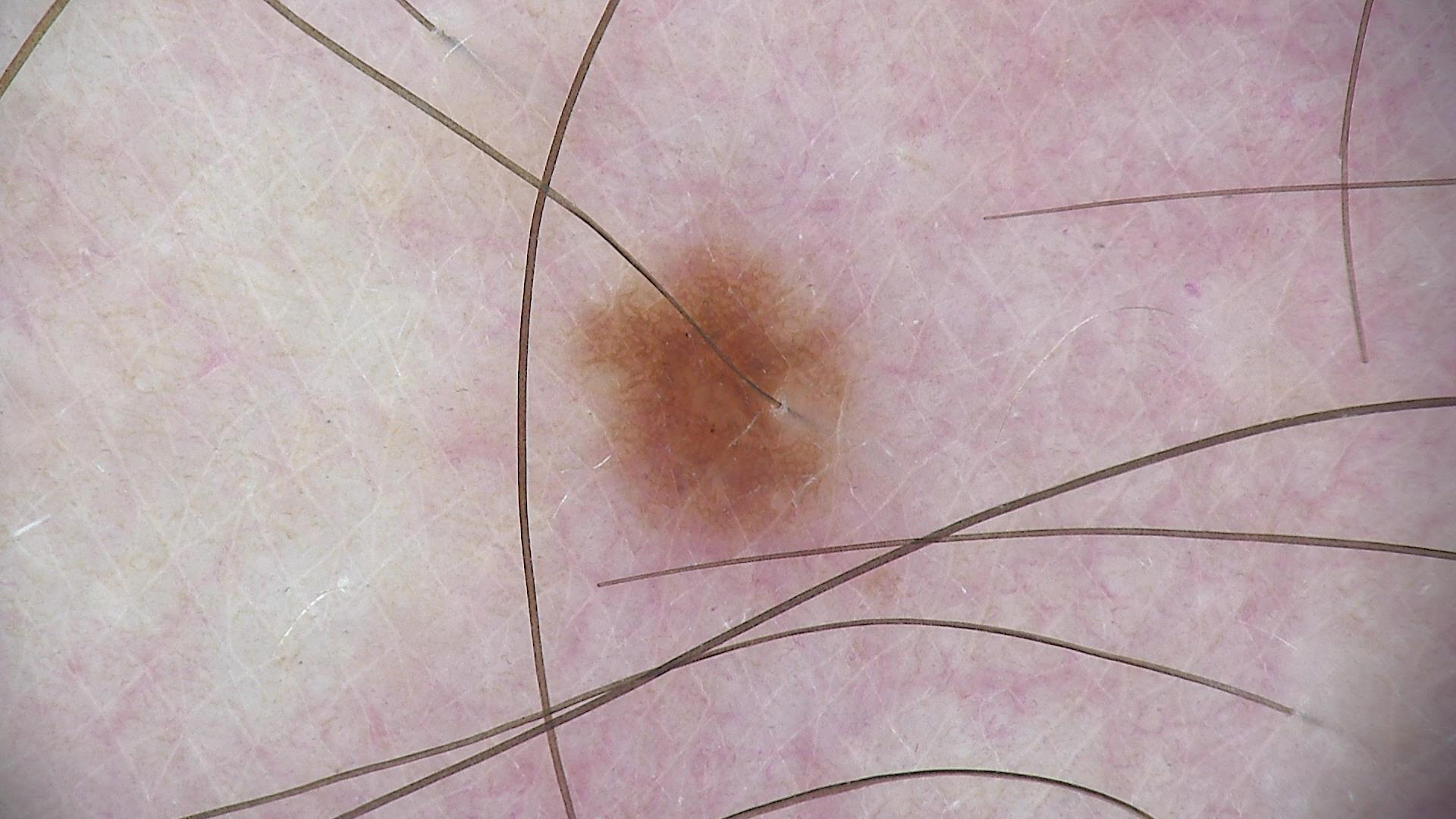A dermoscopy image of a single skin lesion. The diagnosis was a dysplastic junctional nevus.